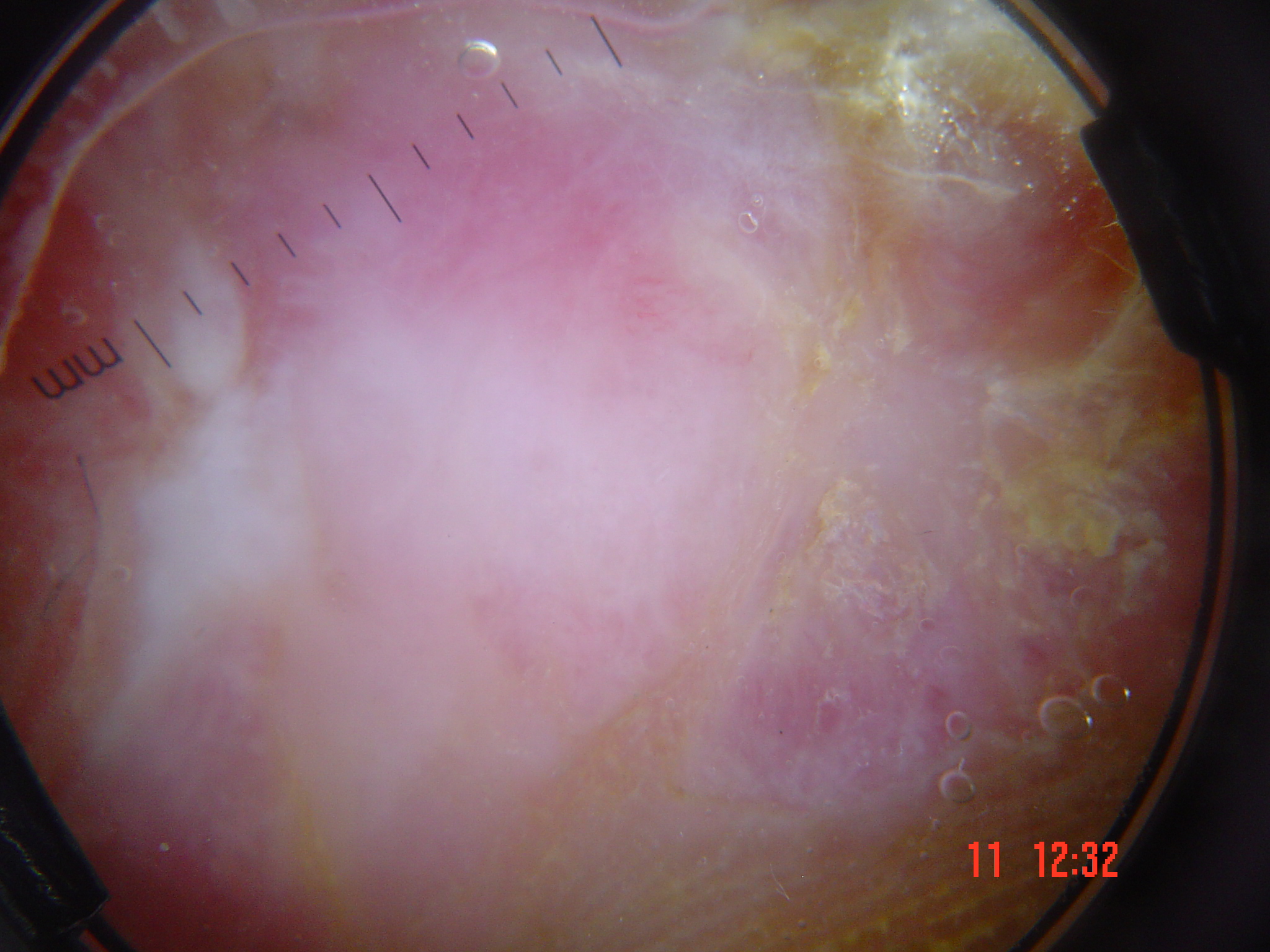A dermoscopic close-up of a skin lesion. Histopathology confirmed a skin cancer — an acral nodular melanoma.